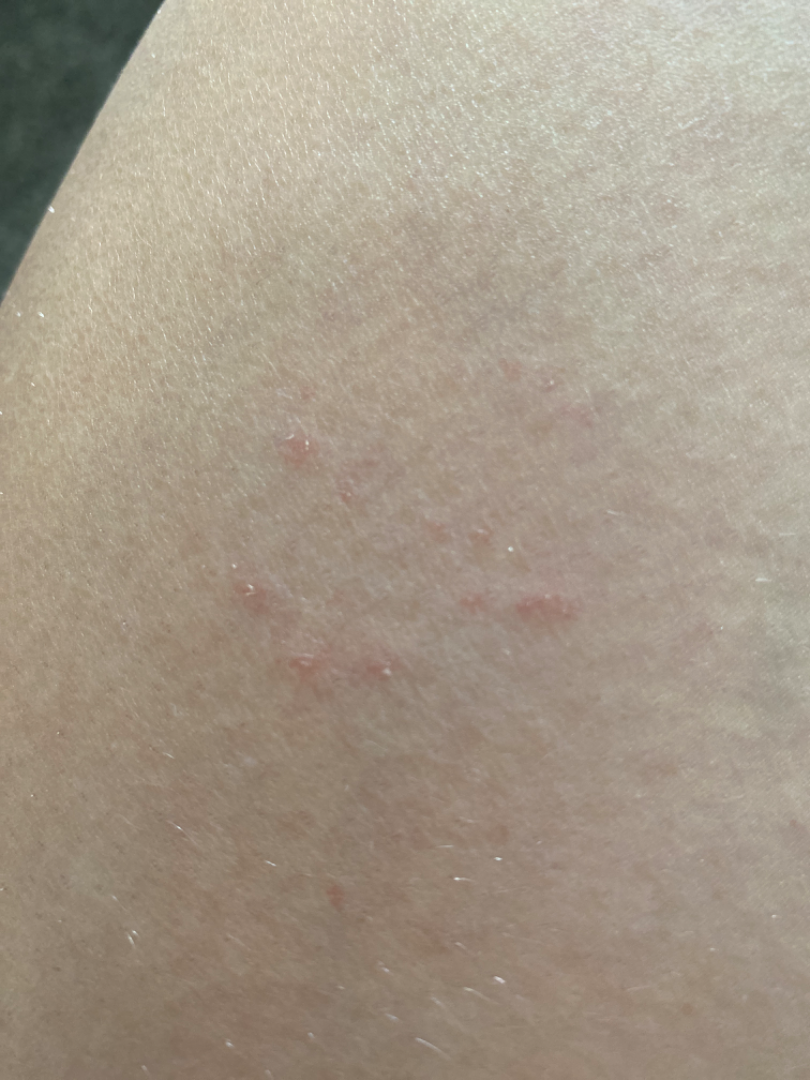Assessment:
The case was indeterminate on photographic review.